This is a dermoscopic photograph of a skin lesion:
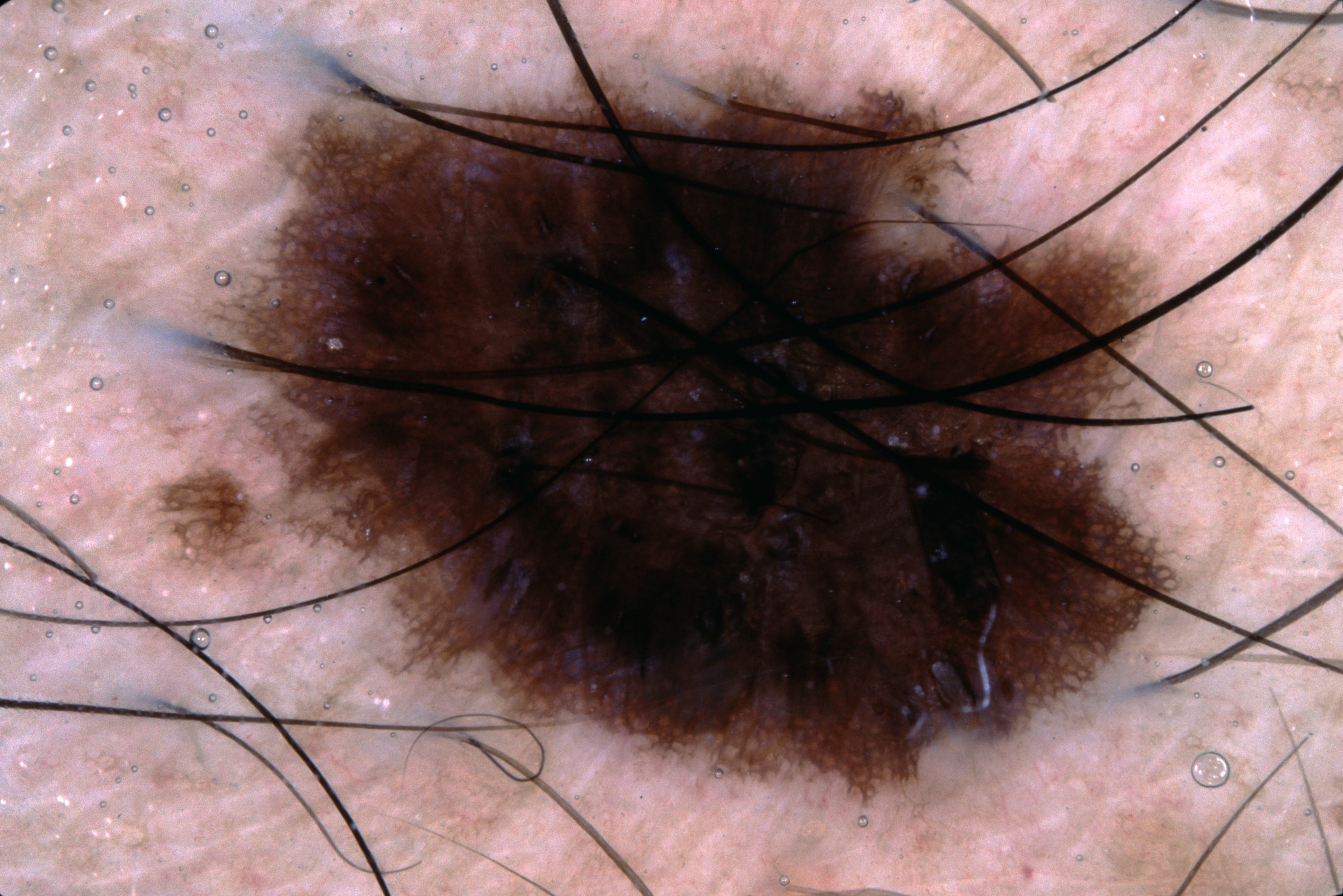Findings:
Dermoscopy demonstrates pigment network. In (x1, y1, x2, y2) order, the lesion is located at 220/70/1175/798.
Conclusion:
Diagnosed as a melanocytic nevus, a benign lesion.